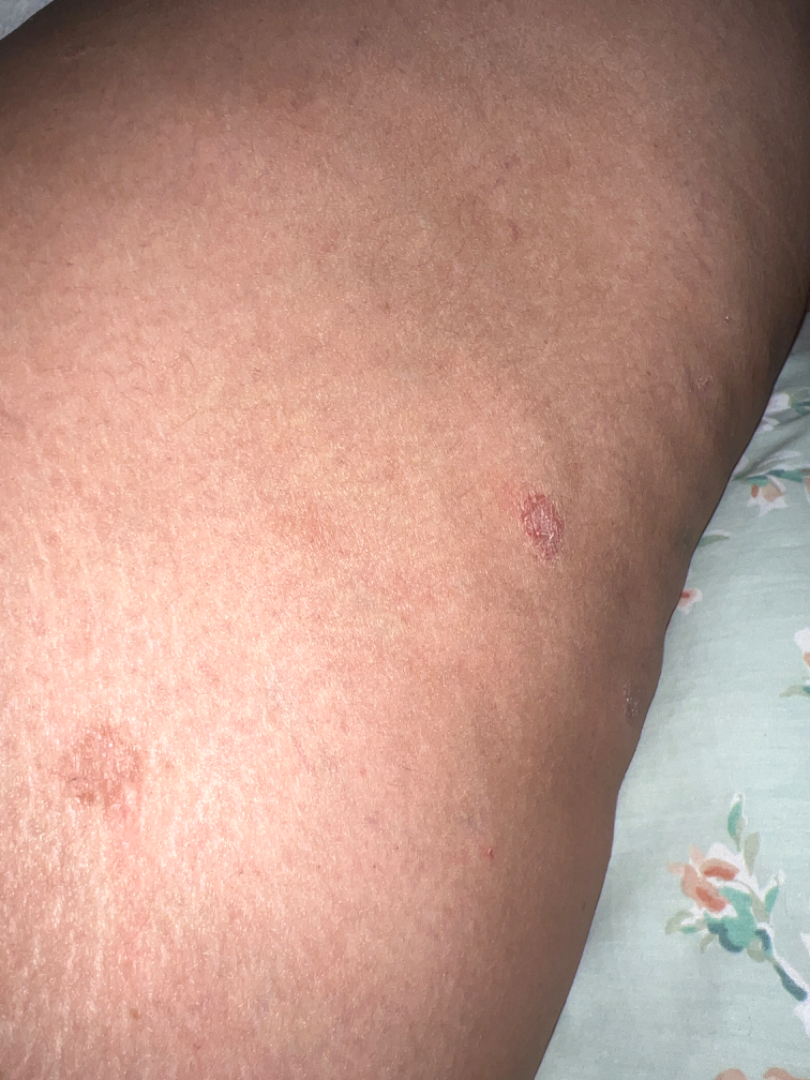Q: What is the affected area?
A: leg
Q: Fitzpatrick or Monk tone?
A: non-clinician graders estimated Monk skin tone scale 2 (US pool) or 4 (India pool)
Q: Patient demographics?
A: female, age 30–39
Q: Patient's own categorization?
A: a rash
Q: Any systemic symptoms?
A: fatigue, joint pain and shortness of breath
Q: Image view?
A: at a distance
Q: What symptoms does the patient report?
A: itching
Q: Texture?
A: rough or flaky
Q: When did this start?
A: more than one year
Q: What conditions are considered?
A: most consistent with Porokeratosis; an alternative is Actinic Keratosis; less likely is SCC/SCCIS